A dermoscopic image of a skin lesion.
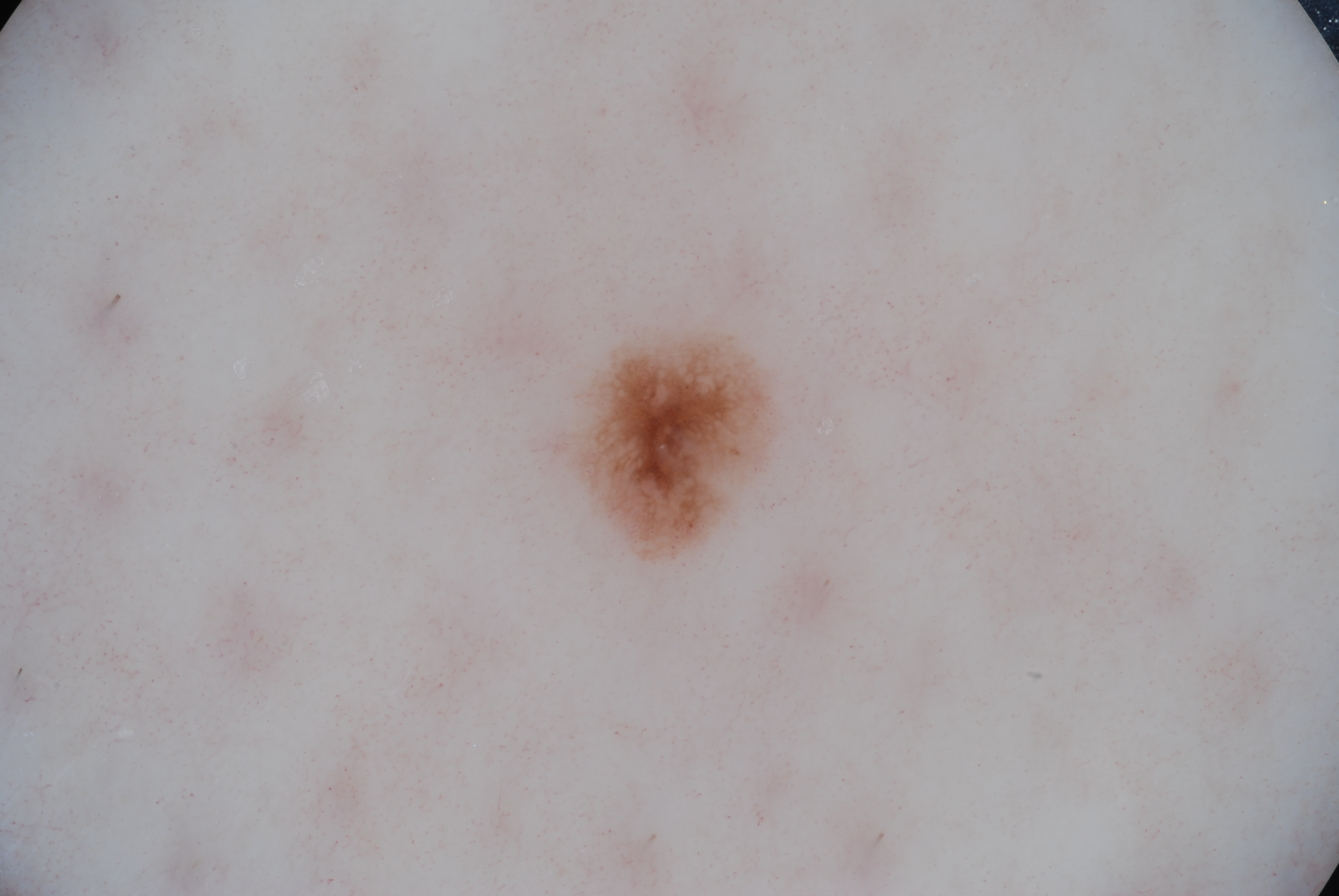– lesion location · bbox(565, 322, 774, 560)
– assessment · a melanocytic nevus, a benign lesion